Close-up view · located on the leg and arm · the patient is male:
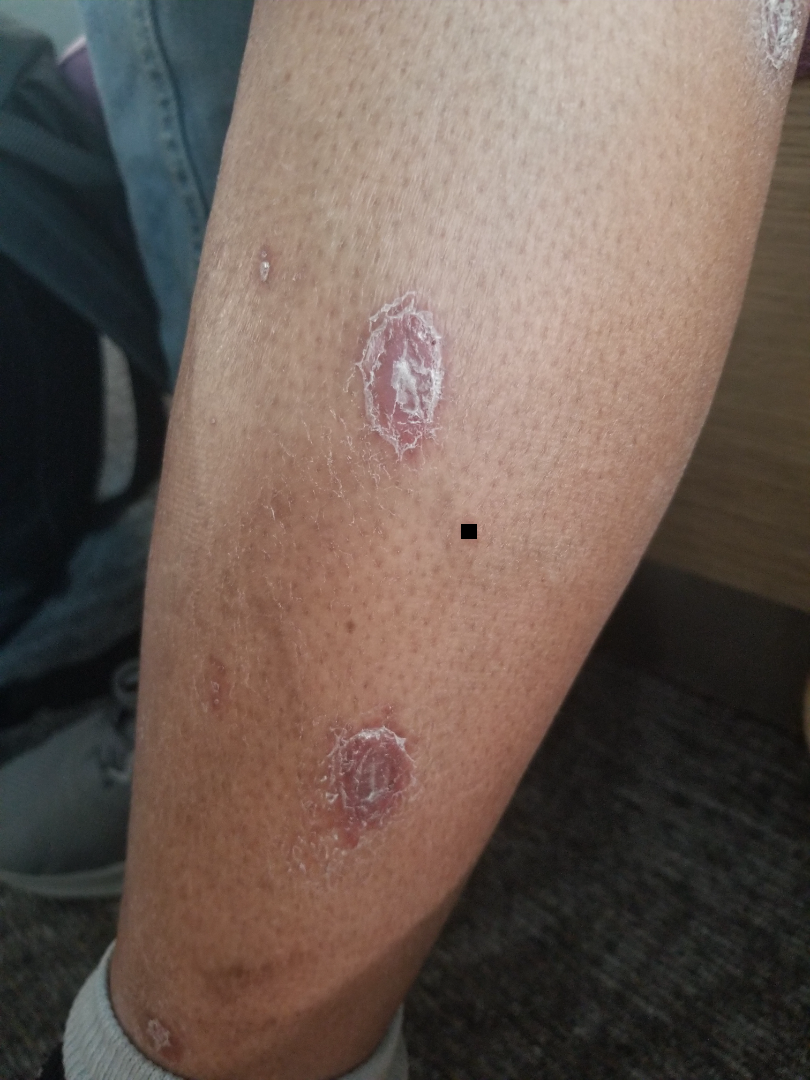Q: What is the differential diagnosis?
A: three dermatologists independently reviewed the case: the leading impression is Psoriasis; the differential also includes Eczema; less probable is Syphilis